Skin tone: lay reviewers estimated 2 on the MST. The patient described the issue as a rash. This is a close-up image. The patient indicates the lesion is raised or bumpy. Male patient, age 50–59. The condition has been present for three to twelve months. Reported lesion symptoms include bothersome appearance, itching and enlargement. The affected area is the leg and top or side of the foot. Associated systemic symptoms include fatigue.
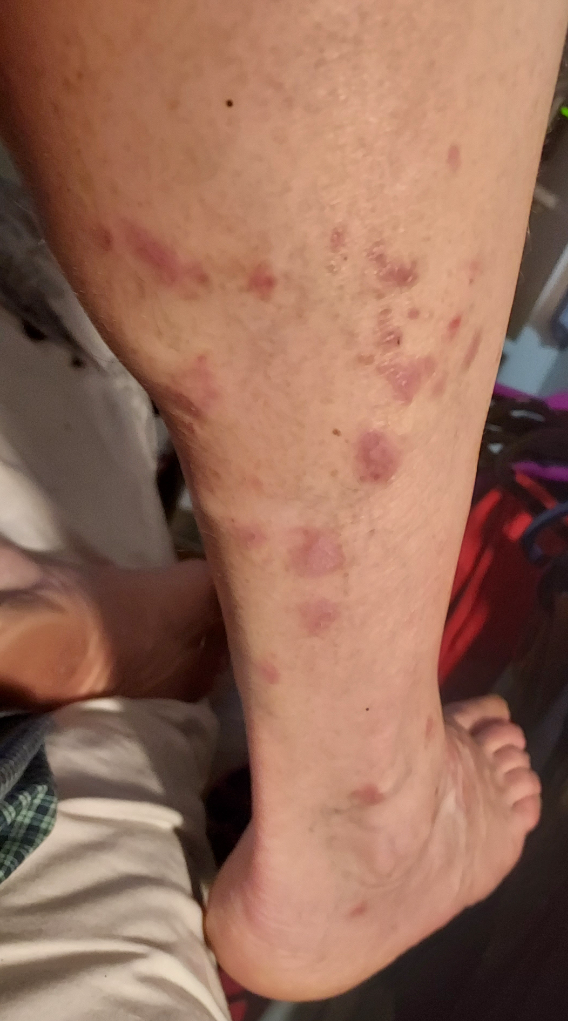Assessment:
Lichen planus/lichenoid eruption and Nodular vasculitis were considered with similar weight; less likely is Psoriasis; a remote consideration is Eczema; less probable is Pseudolymphoma.